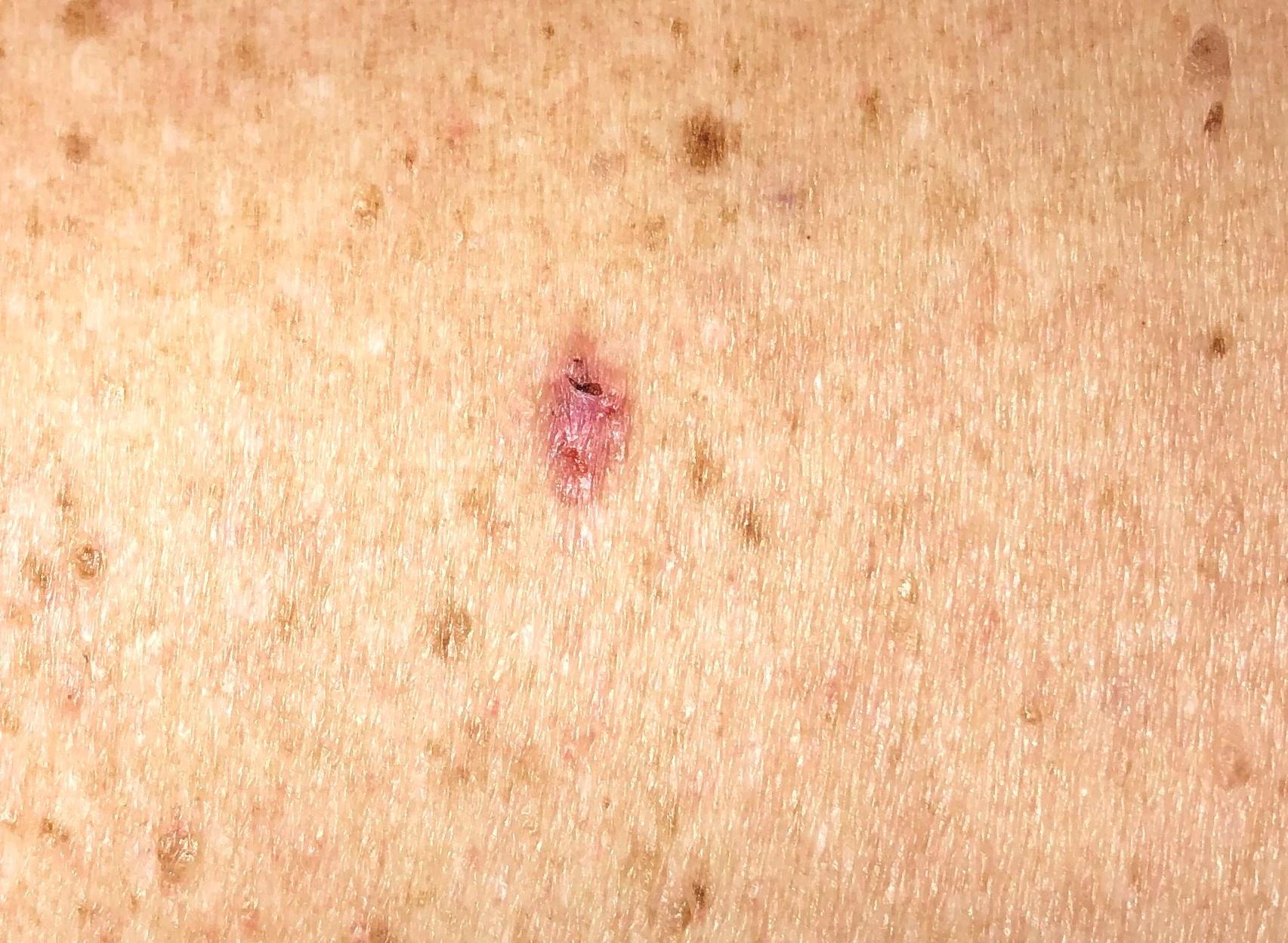diagnostic label = Basal cell carcinoma (biopsy-proven).